The condition has been present for less than one week; the patient described the issue as a rash; the affected area is the arm and head or neck; the patient reports itching; the patient reports the lesion is raised or bumpy; this is a close-up image.
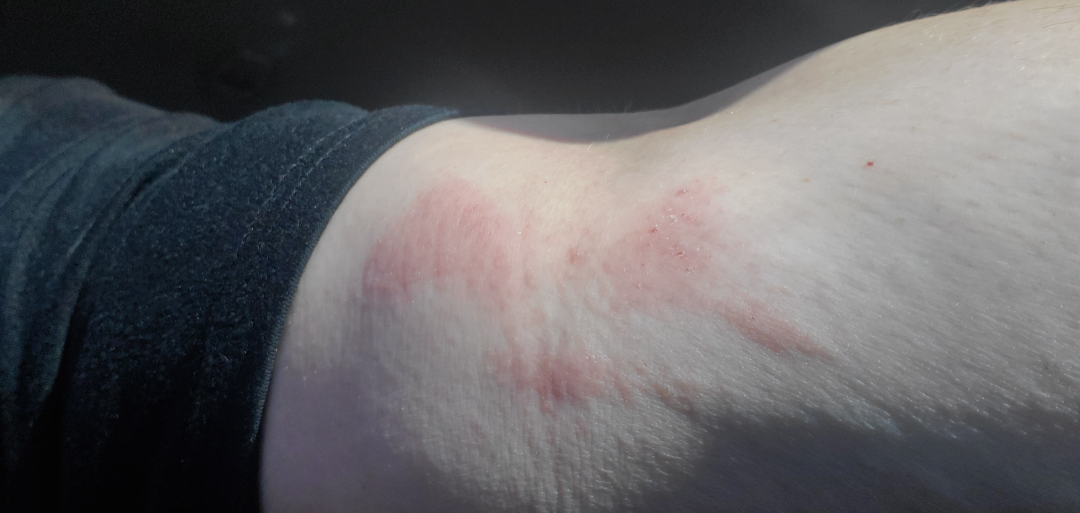Q: What was the assessment?
A: indeterminate from the photograph